The photograph is a close-up of the affected area: 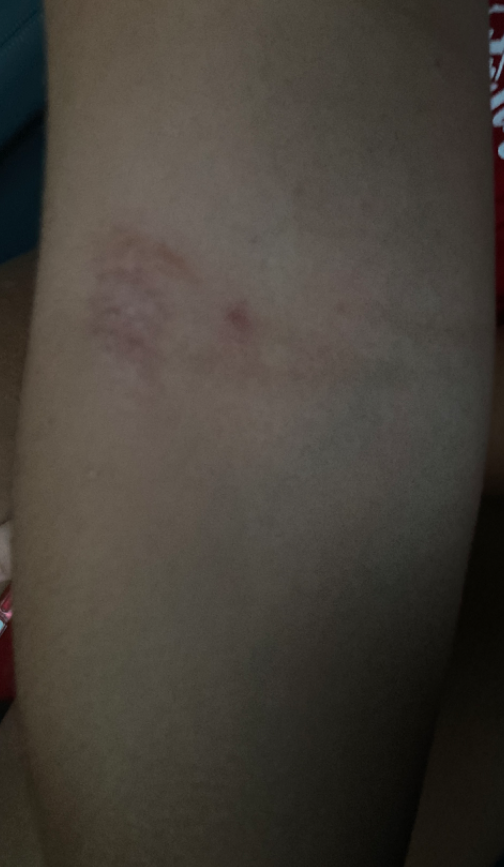On photographic review by a dermatologist, consistent with Eczema.